A dermoscopic close-up of a skin lesion: 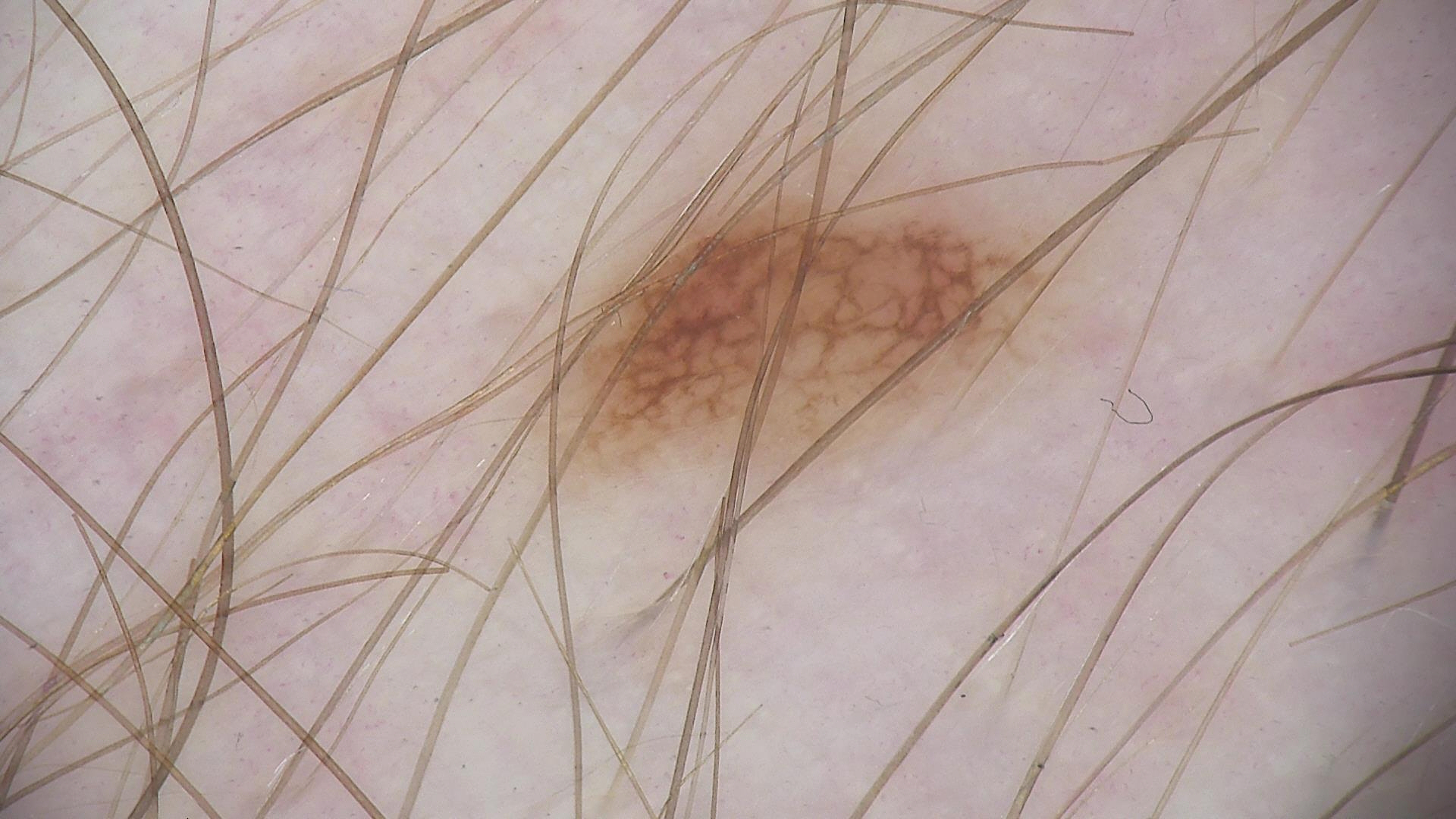diagnostic label — dysplastic junctional nevus (expert consensus)